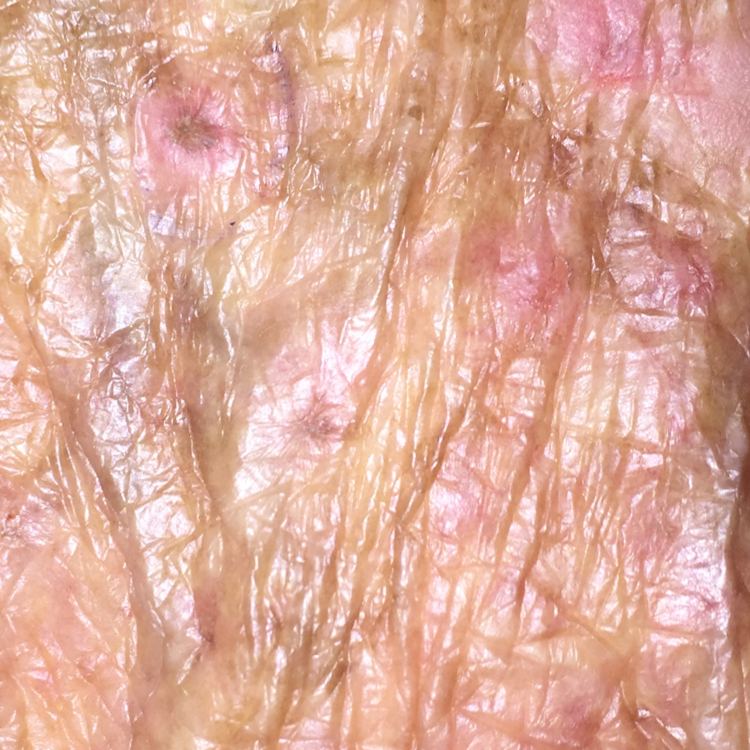{
  "image": "smartphone clinical photo",
  "patient": {
    "age": 60
  },
  "lesion_location": "a forearm",
  "symptoms": {
    "present": [
      "itching",
      "bleeding"
    ],
    "absent": [
      "pain"
    ]
  },
  "diagnosis": {
    "name": "actinic keratosis",
    "code": "ACK",
    "malignancy": "indeterminate",
    "confirmation": "clinical consensus"
  }
}